This is a dermoscopic photograph of a skin lesion:
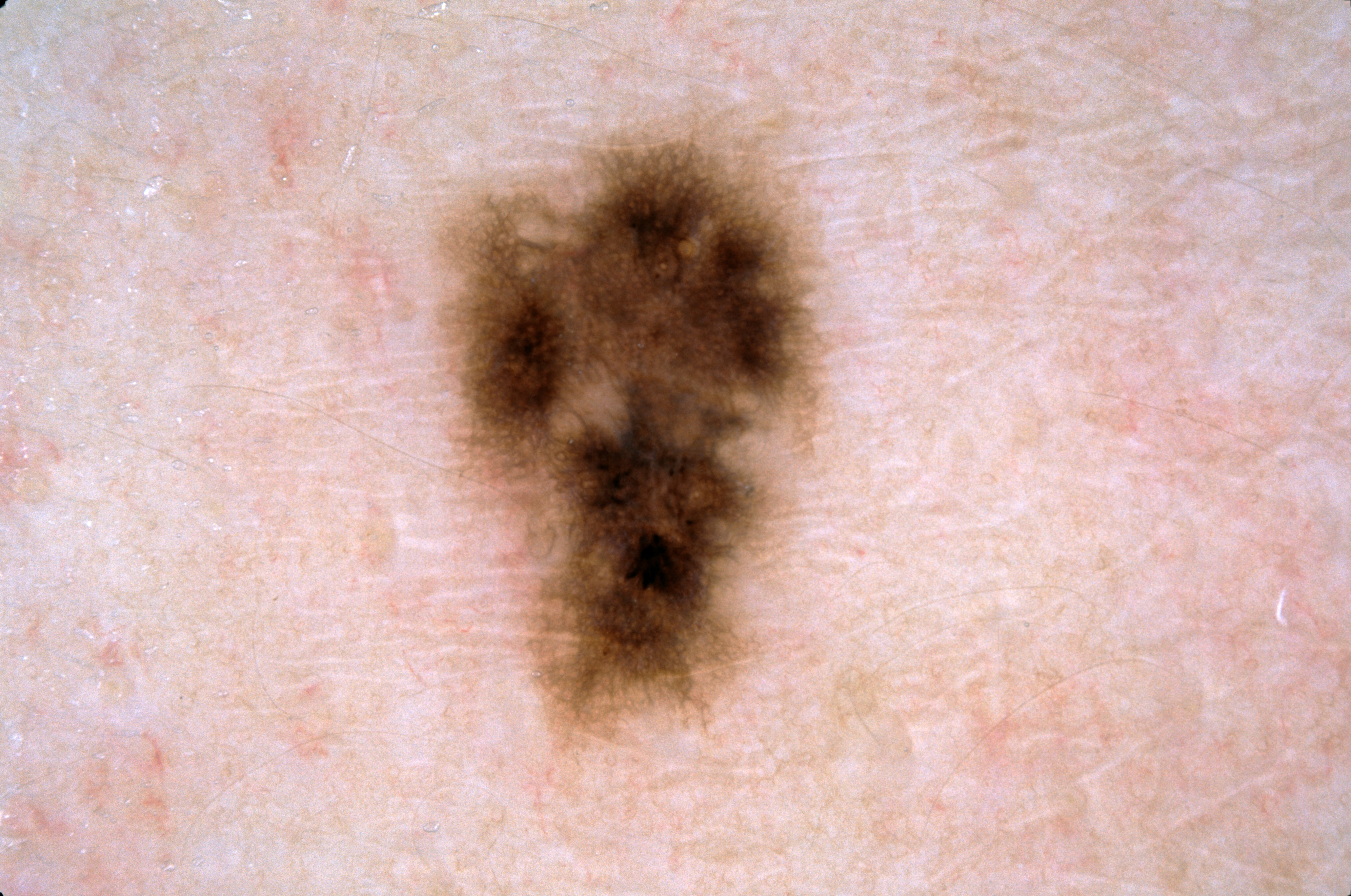Case summary:
On dermoscopy, the lesion shows pigment network. The lesion occupies the region x1=421 y1=83 x2=849 y2=802.
Impression:
Expert review diagnosed this as a melanocytic nevus.